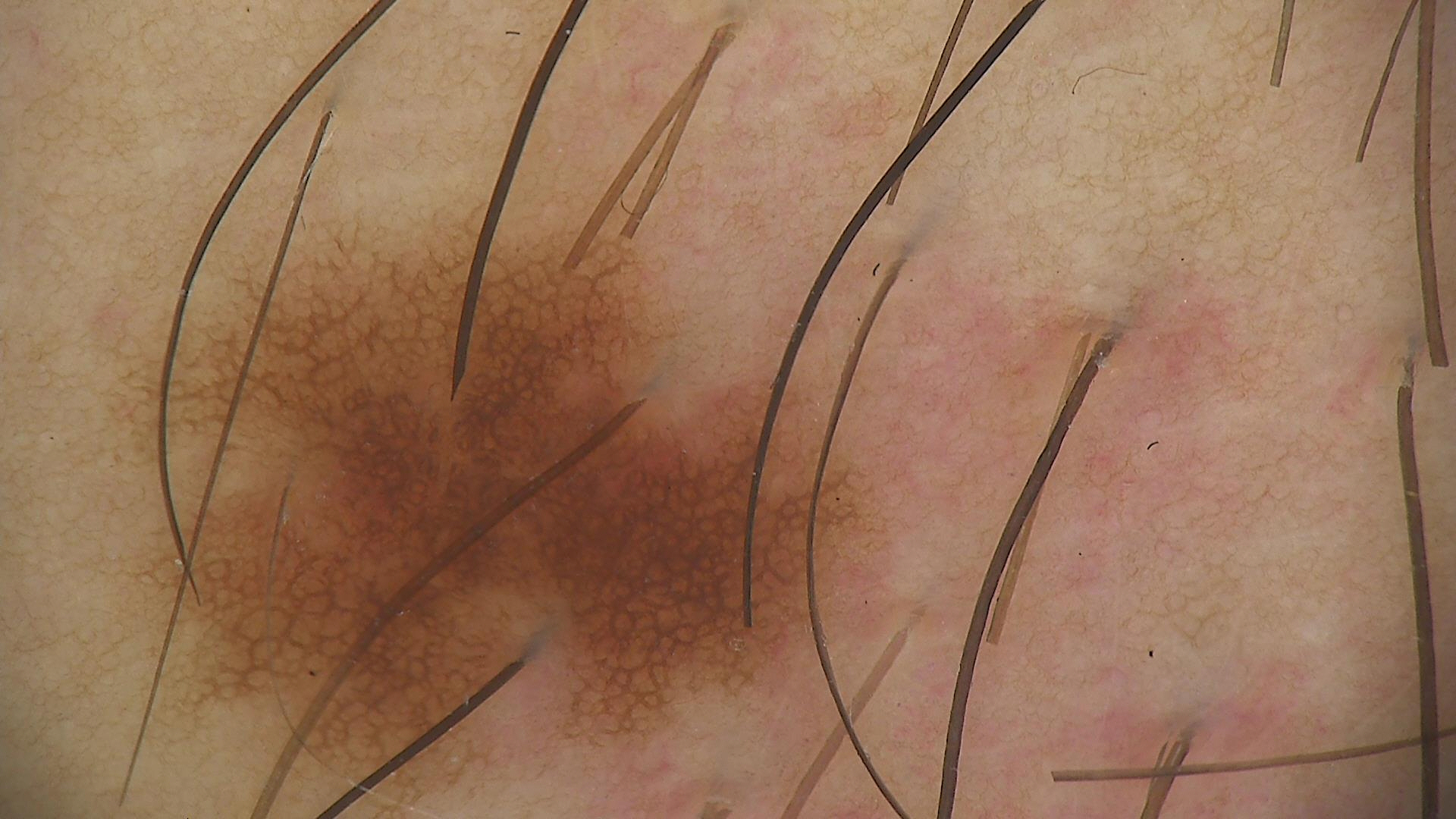Consistent with a benign lesion — a dysplastic junctional nevus.